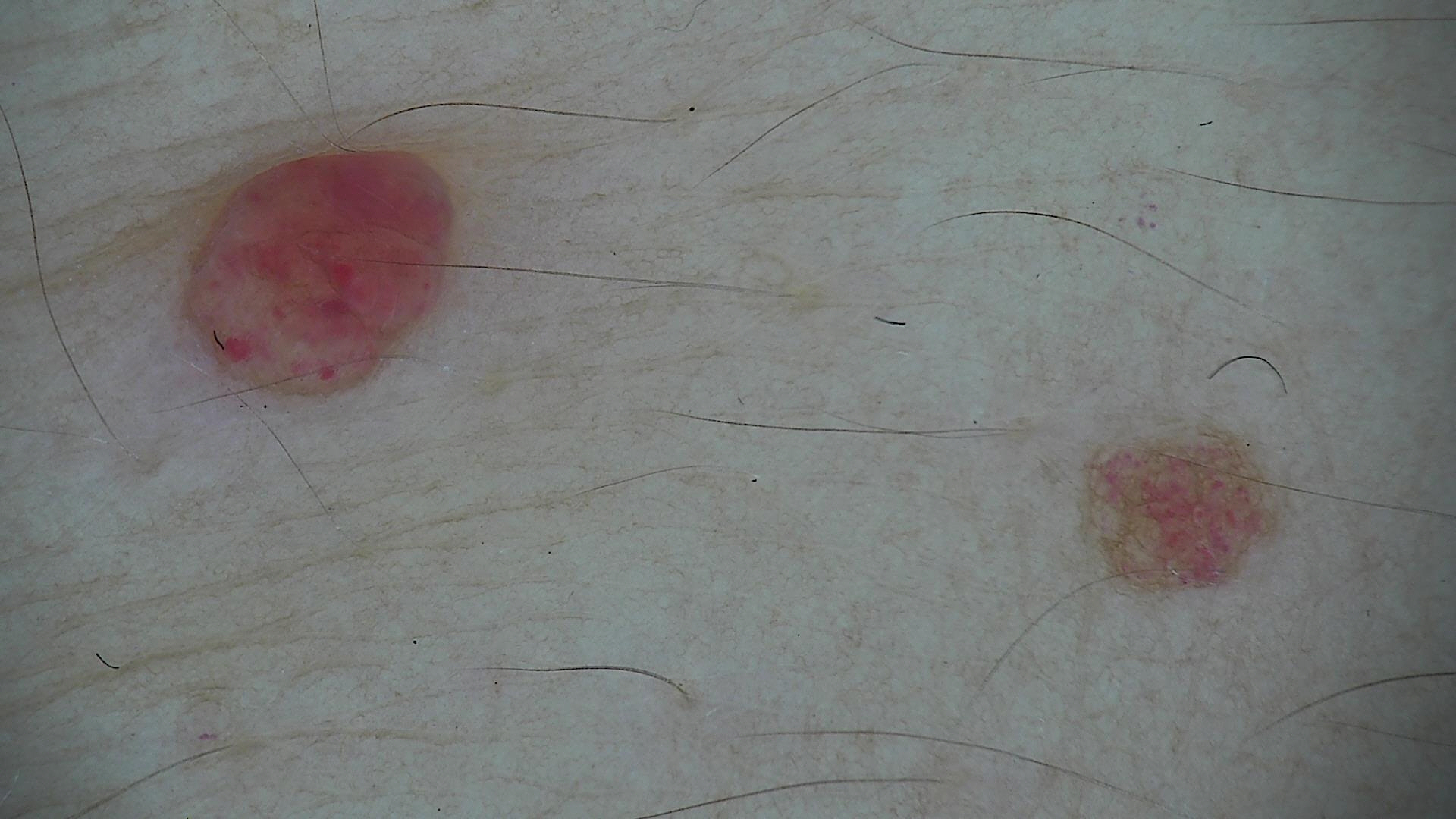• image — dermatoscopy
• lesion type — vascular
• class — hemangioma (expert consensus)